A dermoscopic close-up of a skin lesion: 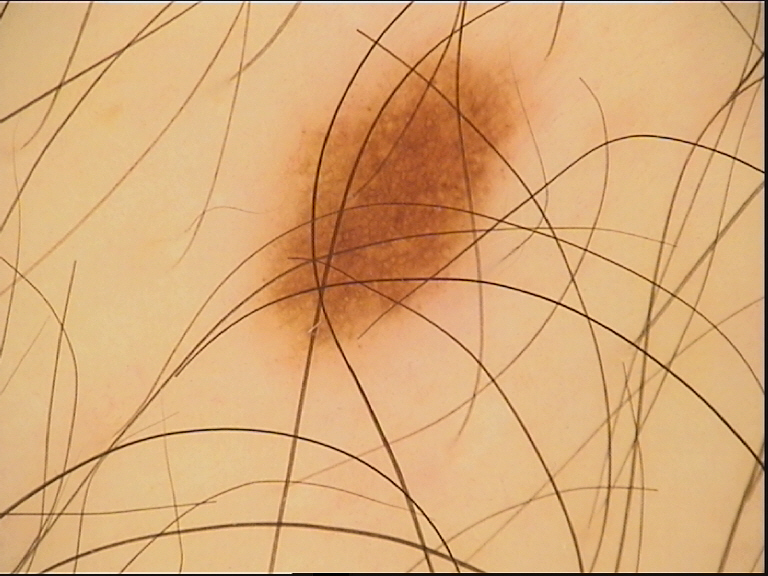diagnostic label: dysplastic junctional nevus (expert consensus)